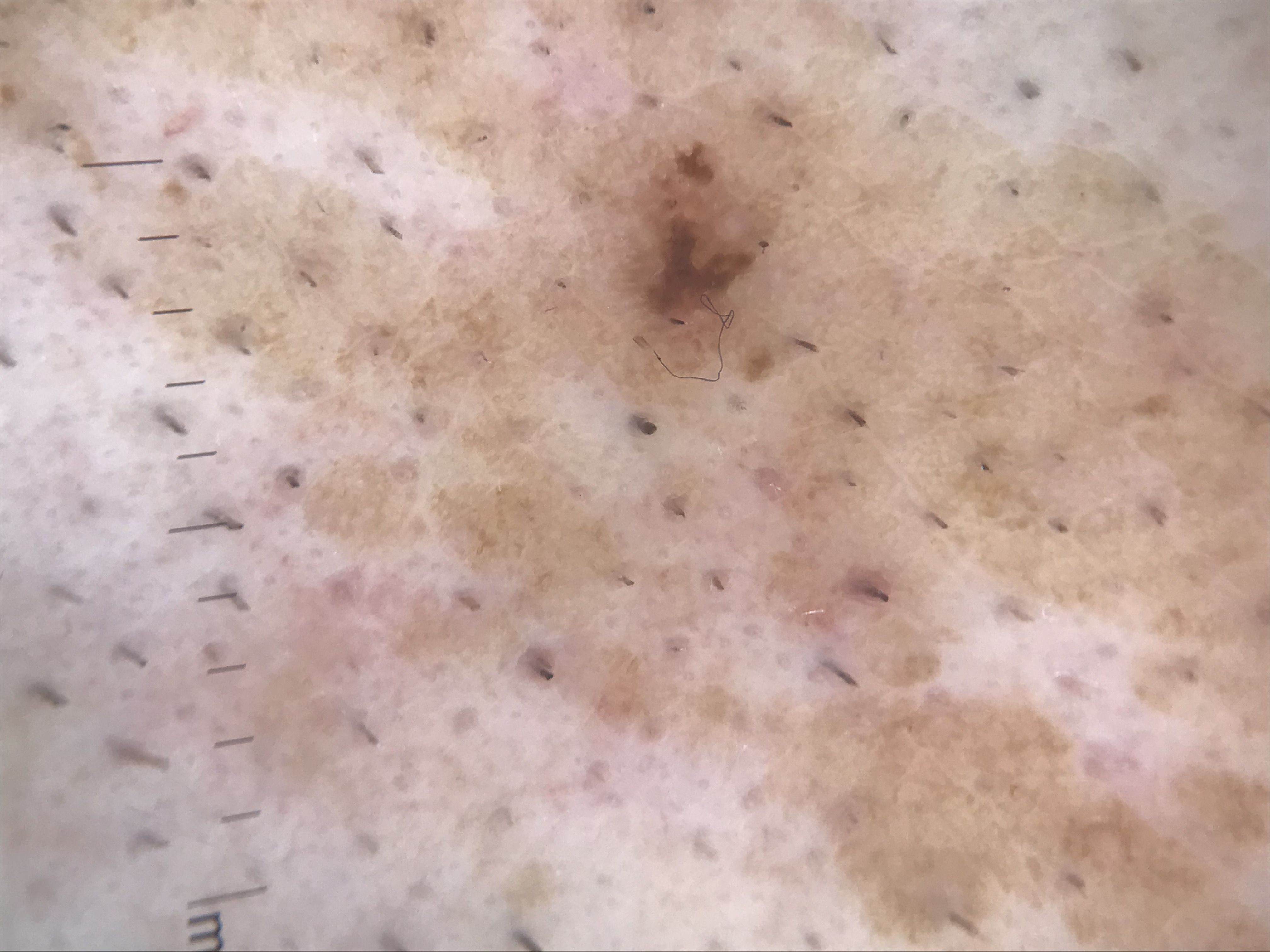imaging: dermatoscopy
diagnosis: seborrheic keratosis (expert consensus)